The affected area is the leg · close-up view:
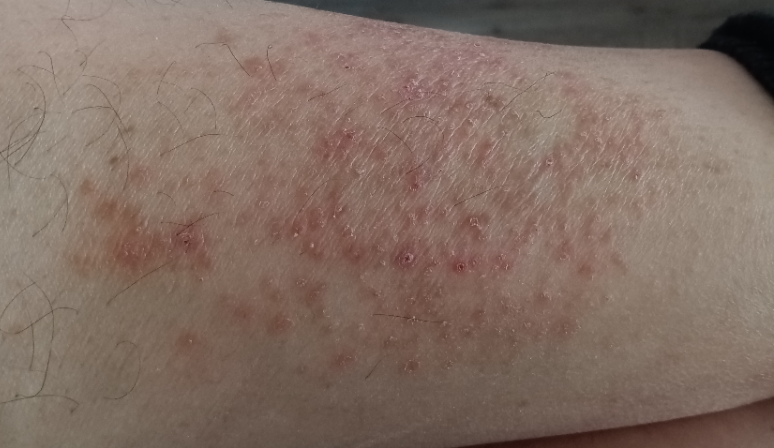Patient information: Texture is reported as raised or bumpy. Review: Eczema (most likely).